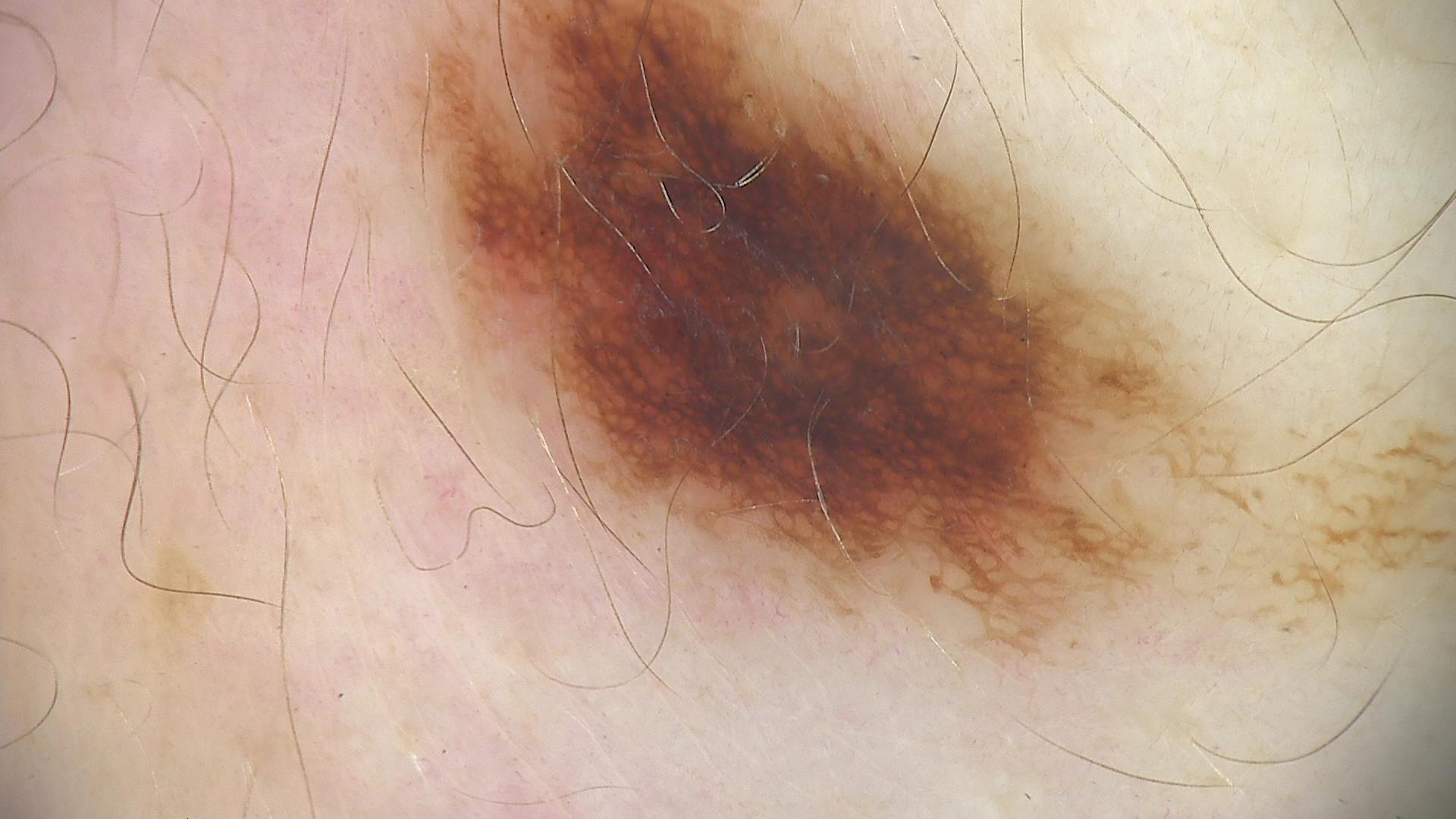Labeled as a benign lesion — a dysplastic junctional nevus.